This is a close-up image; skin tone: Fitzpatrick III; the patient described the issue as a rash; located on the arm; the contributor notes itching; the subject is 18–29, male; the contributor notes the condition has been present for less than one week: 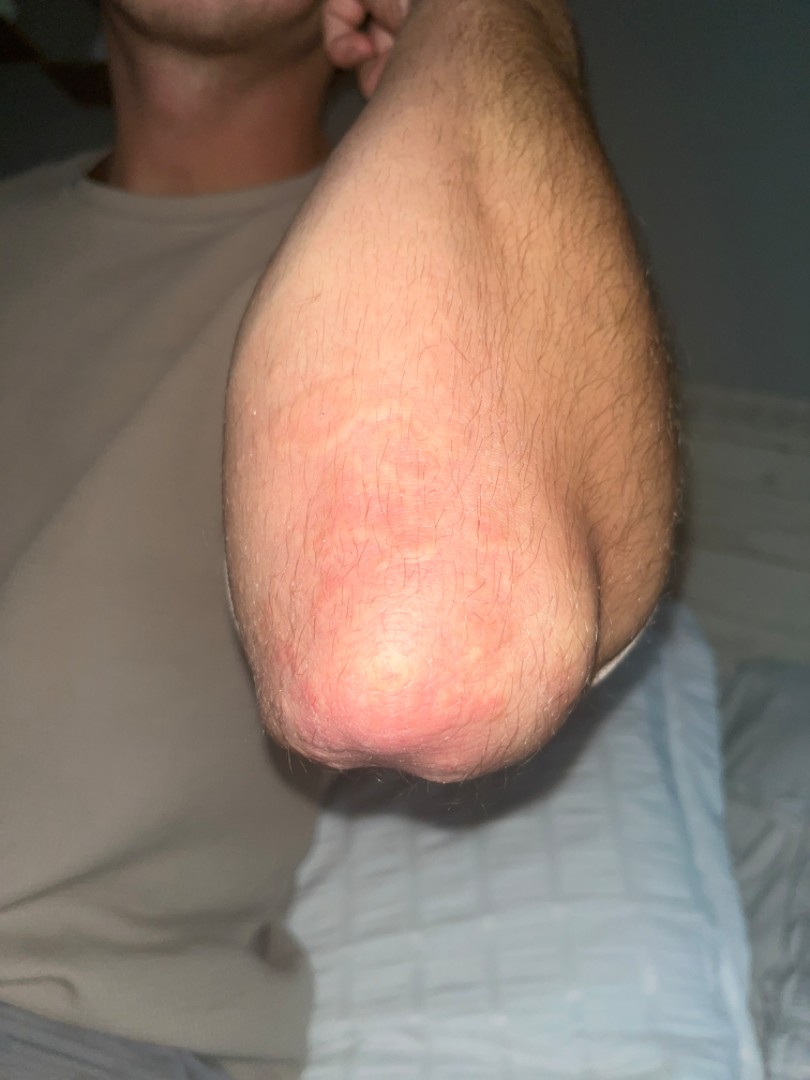The reviewer was unable to grade this case for skin condition.